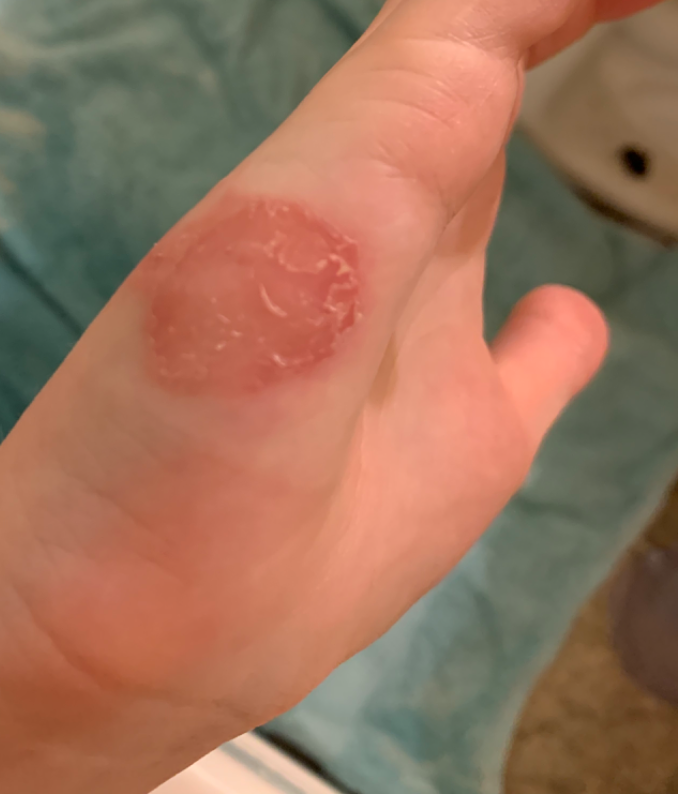Background:
This is a close-up image. The lesion involves the back of the hand and palm. Reported lesion symptoms include burning, itching, enlargement and pain. The contributor notes the condition has been present for three to twelve months. The patient considered this a rash. The contributor notes the lesion is rough or flaky. Skin tone: Fitzpatrick phototype I. The contributor is a female aged 18–29.
Findings:
The reviewing panel's impression was: most likely Psoriasis; an alternative is Irritant Contact Dermatitis; less probable is Tinea; less likely is Eczema; a more distant consideration is Burn erythema of back of hand.